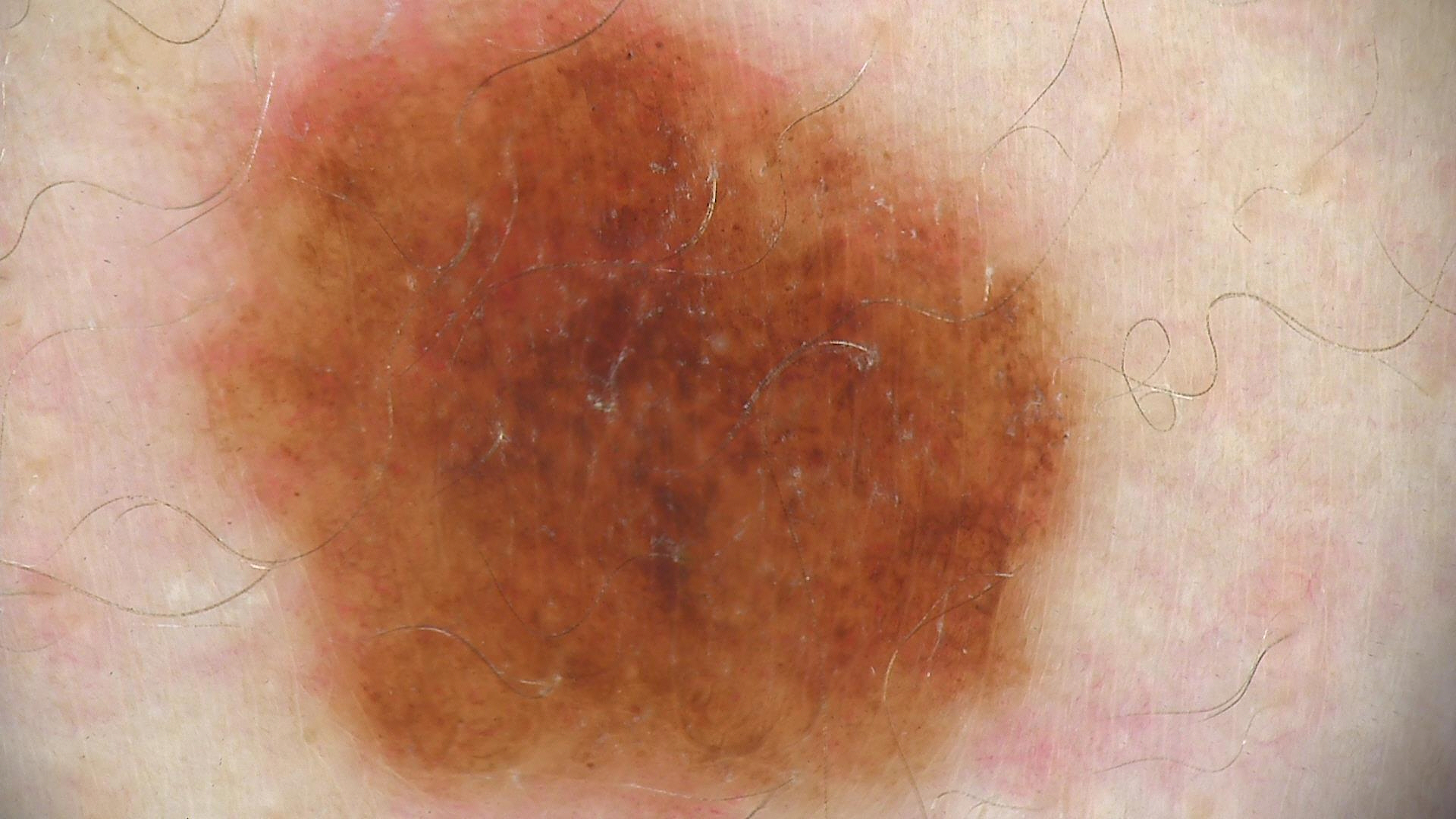Dermoscopy of a skin lesion. The diagnostic label was a benign lesion — a dysplastic junctional nevus.